A skin lesion imaged with a dermatoscope:
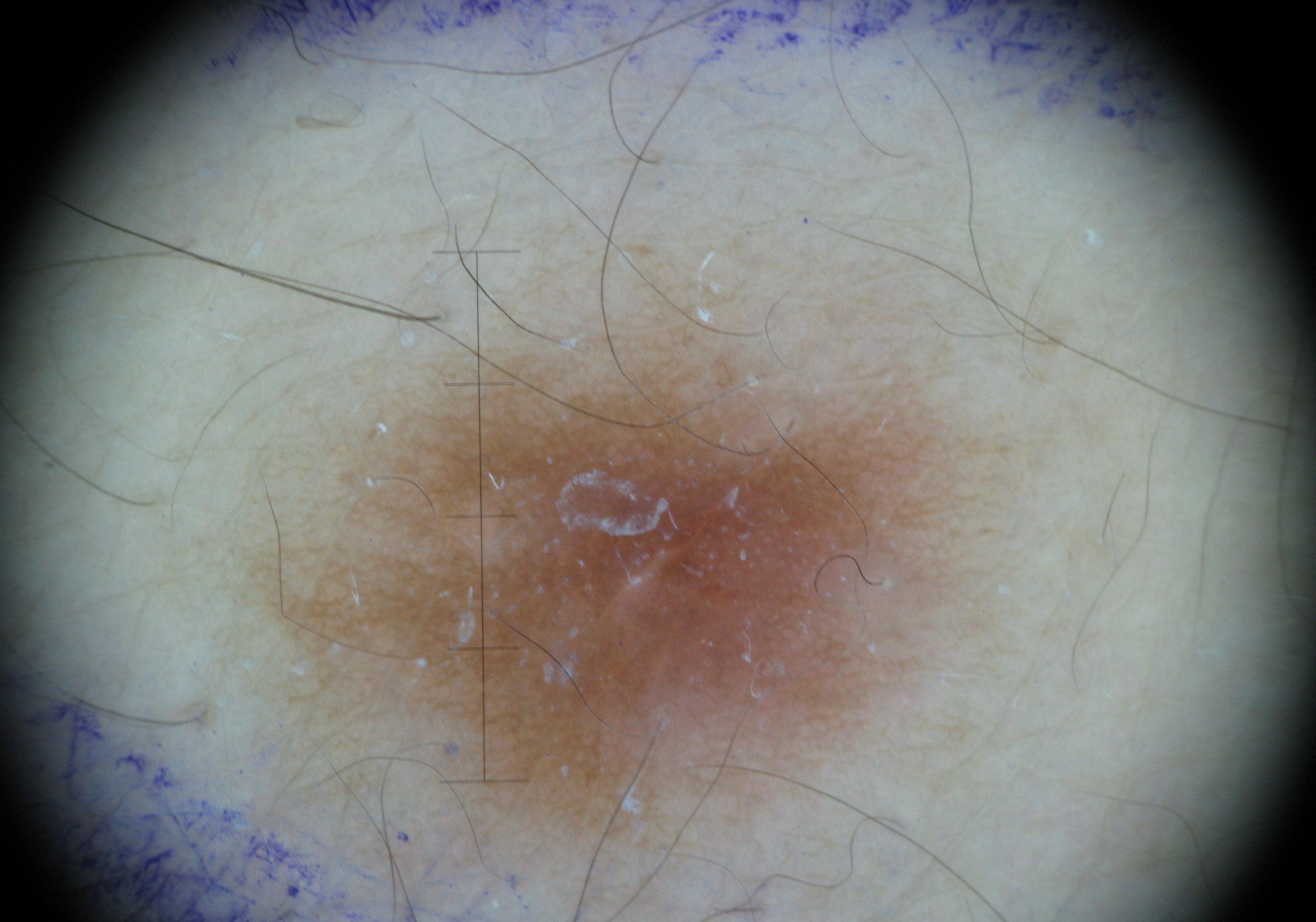Findings:
• assessment — dermatofibroma (expert consensus)